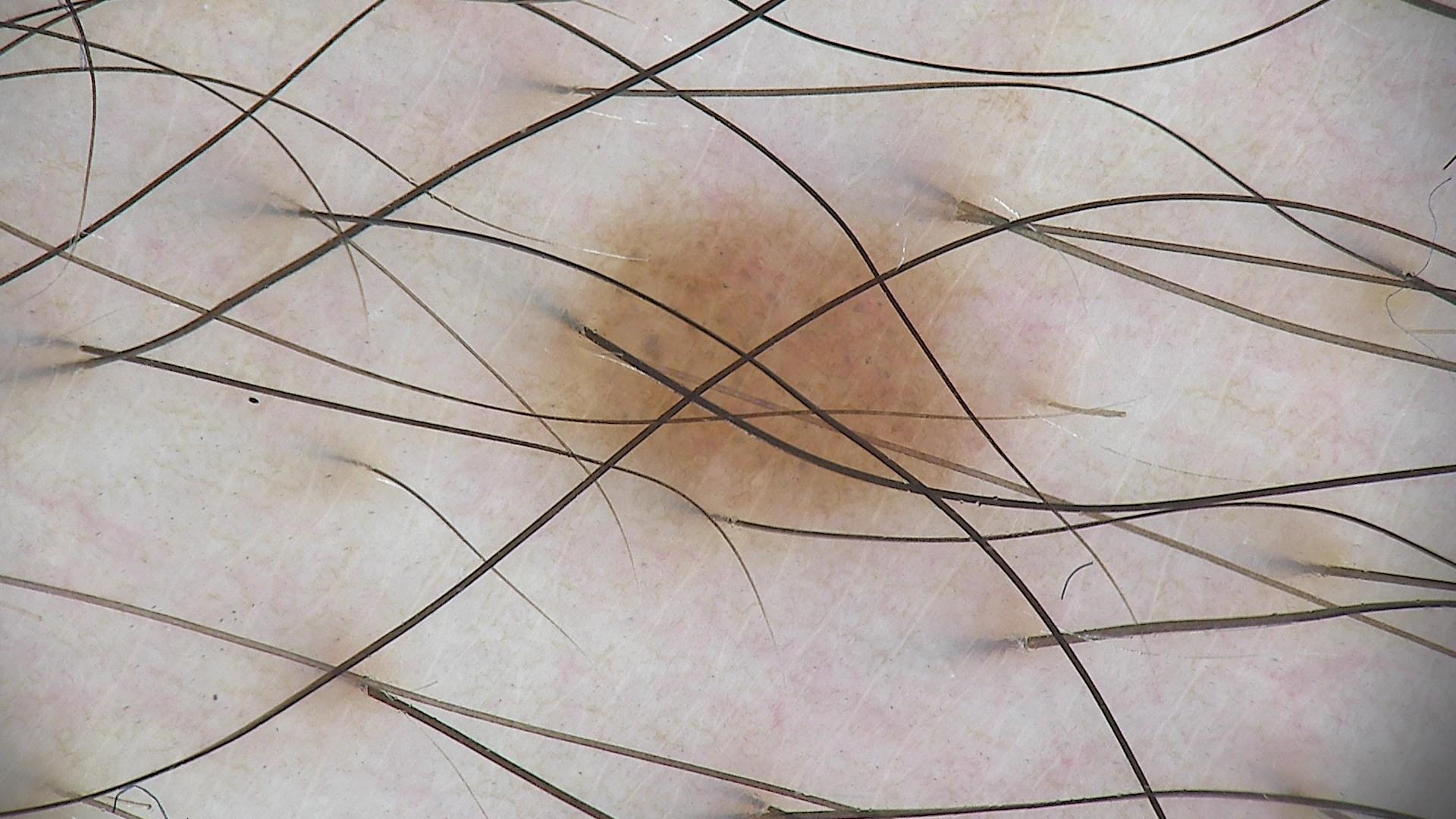Impression: Classified as a dysplastic junctional nevus.